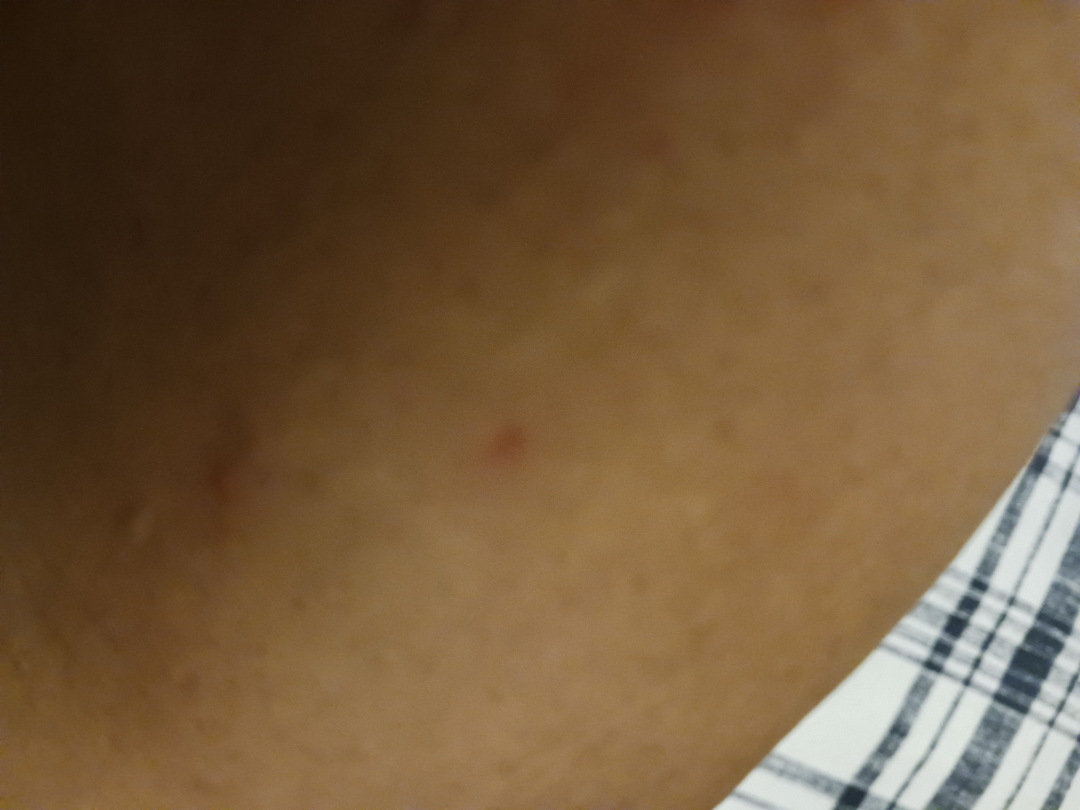The skin findings could not be characterized from the image. The affected area is the arm. The photograph is a close-up of the affected area.